A dermoscopic photograph of a skin lesion.
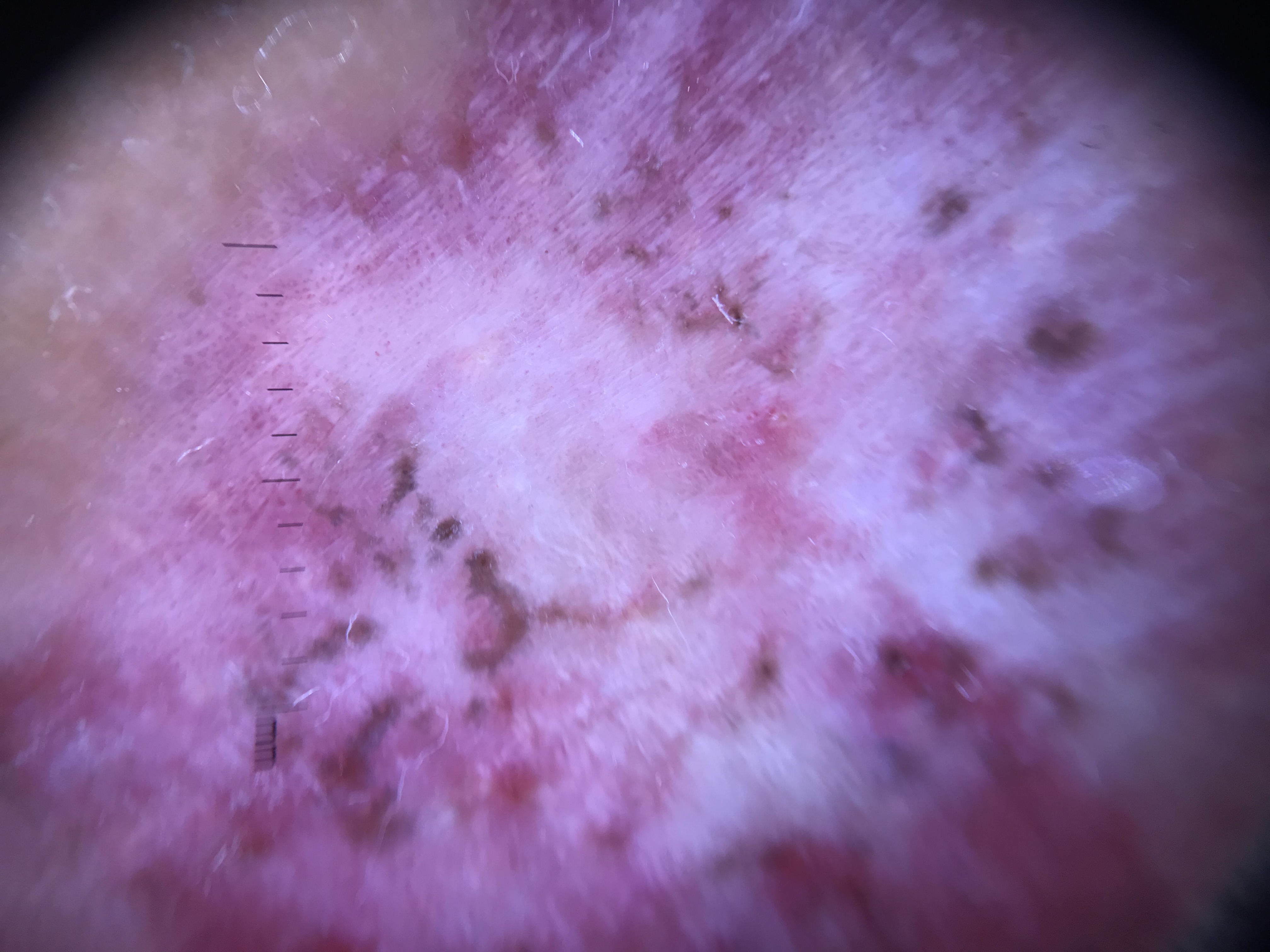Diagnosis:
Confirmed on histopathology as a skin cancer — a basal cell carcinoma.